A skin lesion imaged with a dermatoscope.
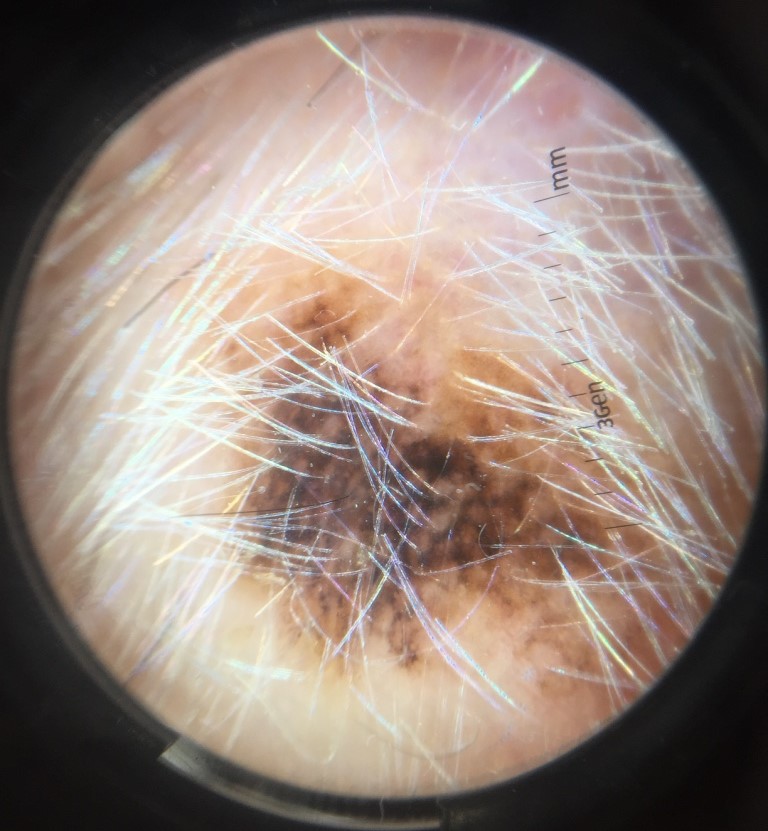Biopsy-confirmed as a melanoma.